This is a dermoscopic photograph of a skin lesion.
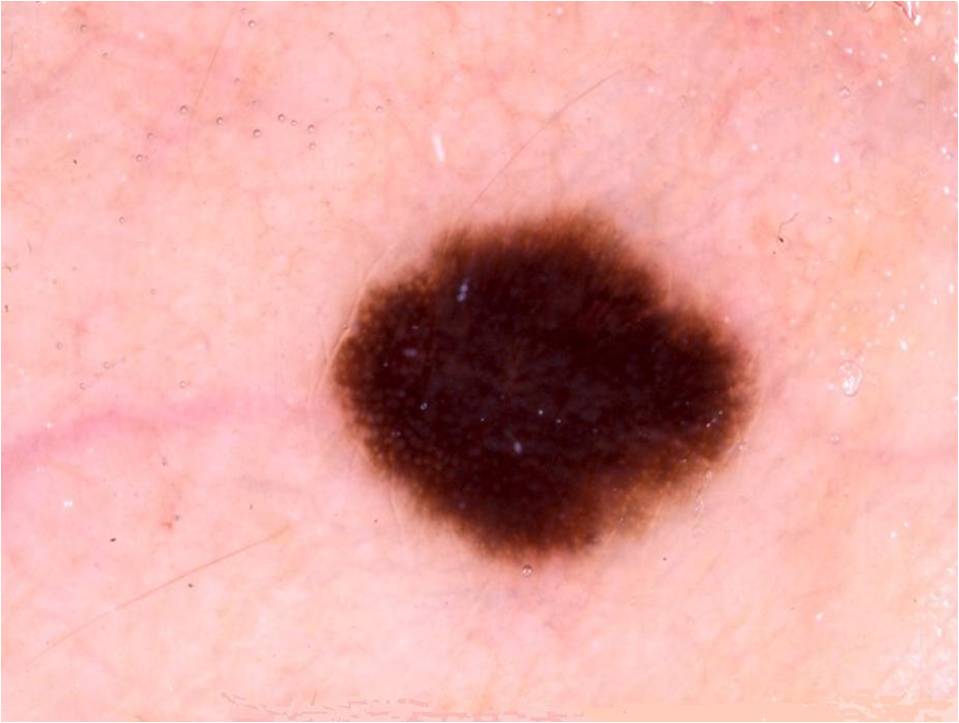bounding box = left=326, top=202, right=757, bottom=570
dermoscopic findings = pigment network; absent: negative network, streaks, globules, and milia-like cysts
diagnostic label = a melanocytic nevus